The referring clinician suspected melanocytic nevus · the patient reports no immunosuppression · a female subject 15 years of age · a clinical photograph of a skin lesion · few moles overall by the patient's own estimate · the patient says their skin reddens with sun exposure — 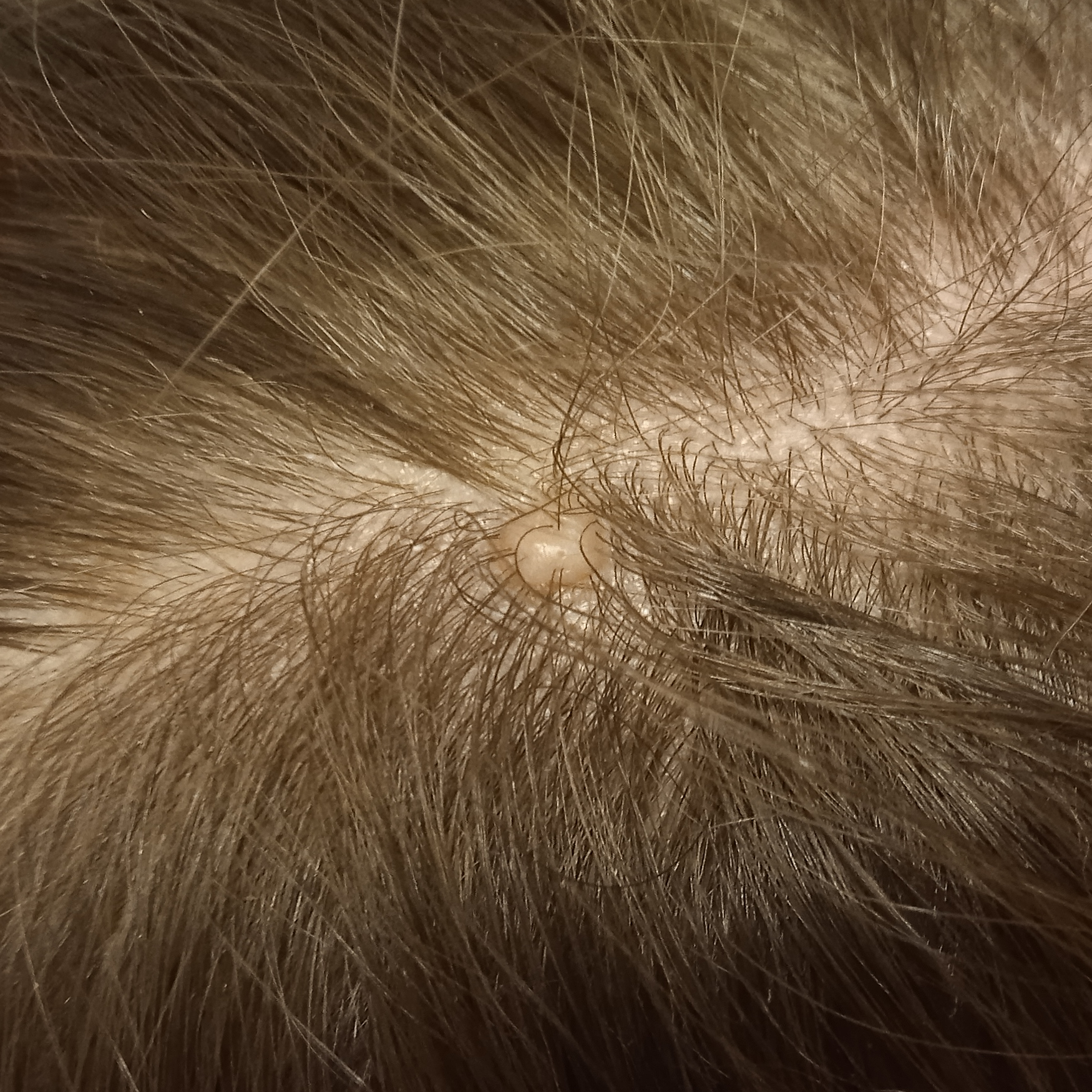<lesion>
<lesion_location>the head</lesion_location>
<lesion_size>
<diameter_mm>5.0</diameter_mm>
</lesion_size>
<diagnosis>
<name>melanocytic nevus</name>
<malignancy>benign</malignancy>
<procedure>excision</procedure>
</diagnosis>
</lesion>